The photograph was taken at a distance · located on the back of the hand — 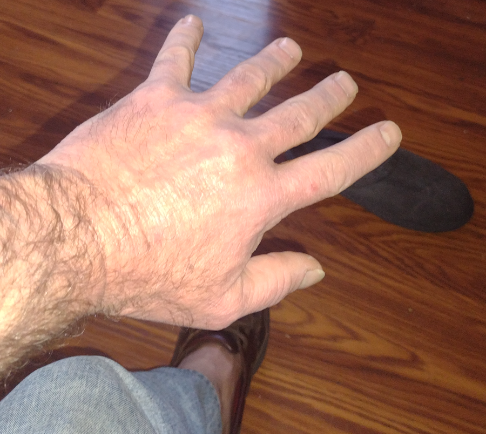The dermatologist found no clearly identifiable skin pathology in the image.